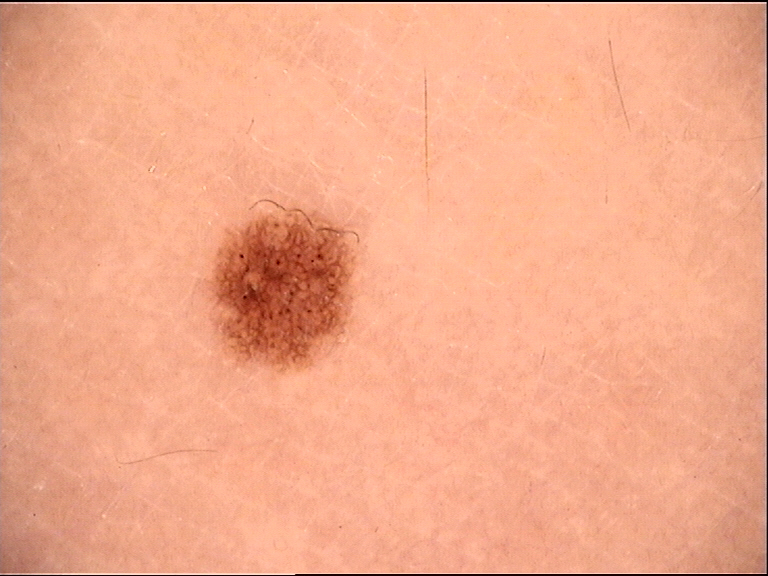Q: What is the imaging modality?
A: dermatoscopy
Q: What is the diagnosis?
A: dysplastic junctional nevus (expert consensus)